This image was taken at a distance: 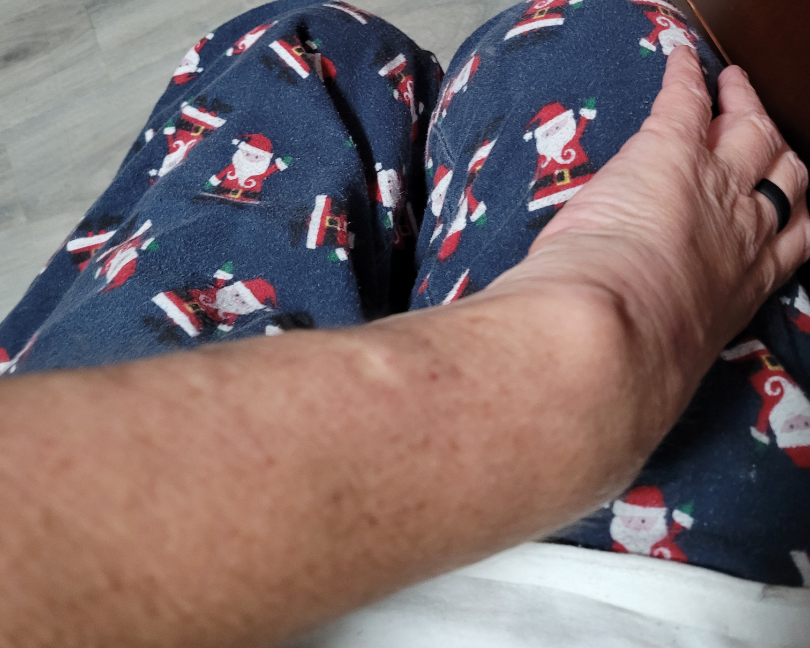assessment: unable to determine.